The patient is 50–59, male; close-up view; the back of the torso and leg are involved: 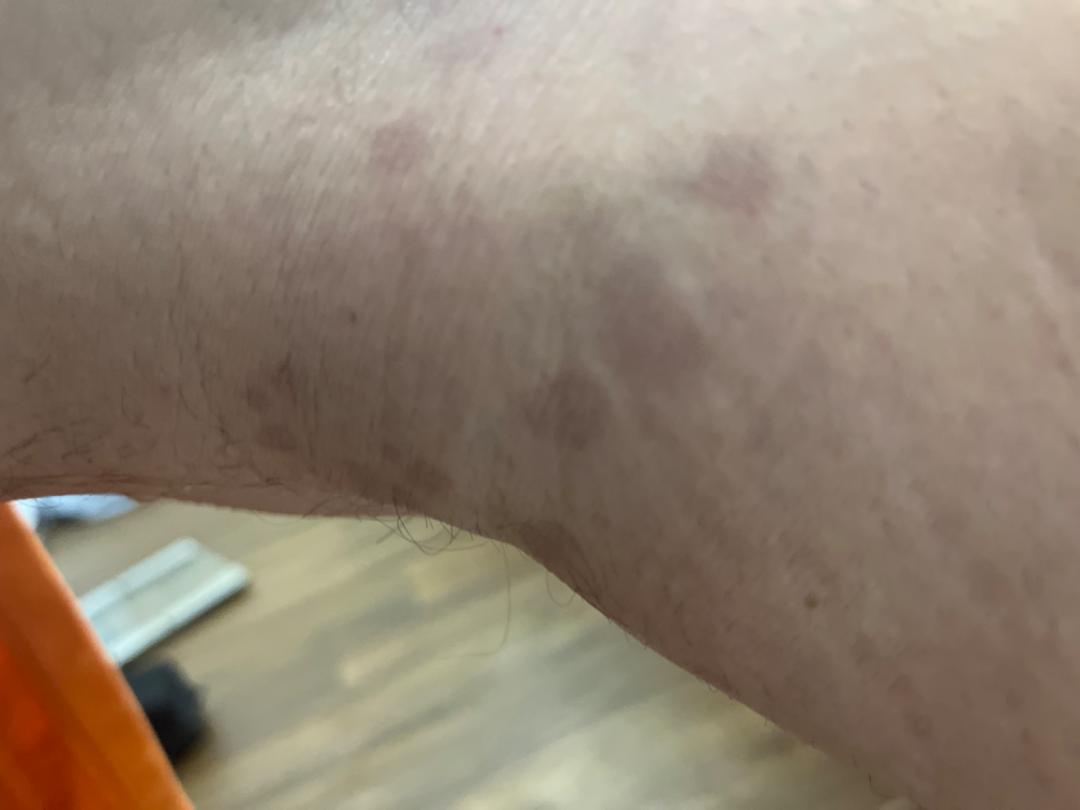  assessment: not assessable
  symptoms:
    - bothersome appearance
    - darkening
  duration: one to three months
  patient_category: a rash
  texture: raised or bumpy